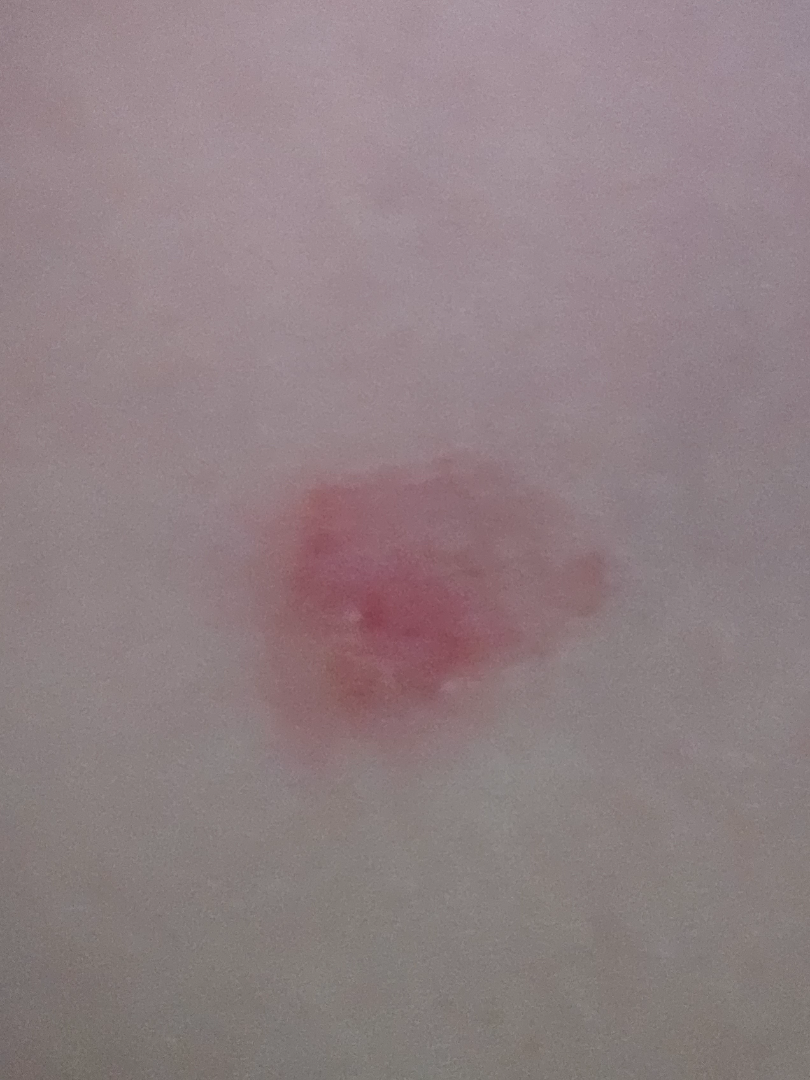assessment = ungradable on photographic review, reported symptoms = itching and bothersome appearance, self-categorized as = a rash, image framing = at a distance, onset = one to four weeks, lesion texture = rough or flaky.